A dermoscopic close-up of a skin lesion.
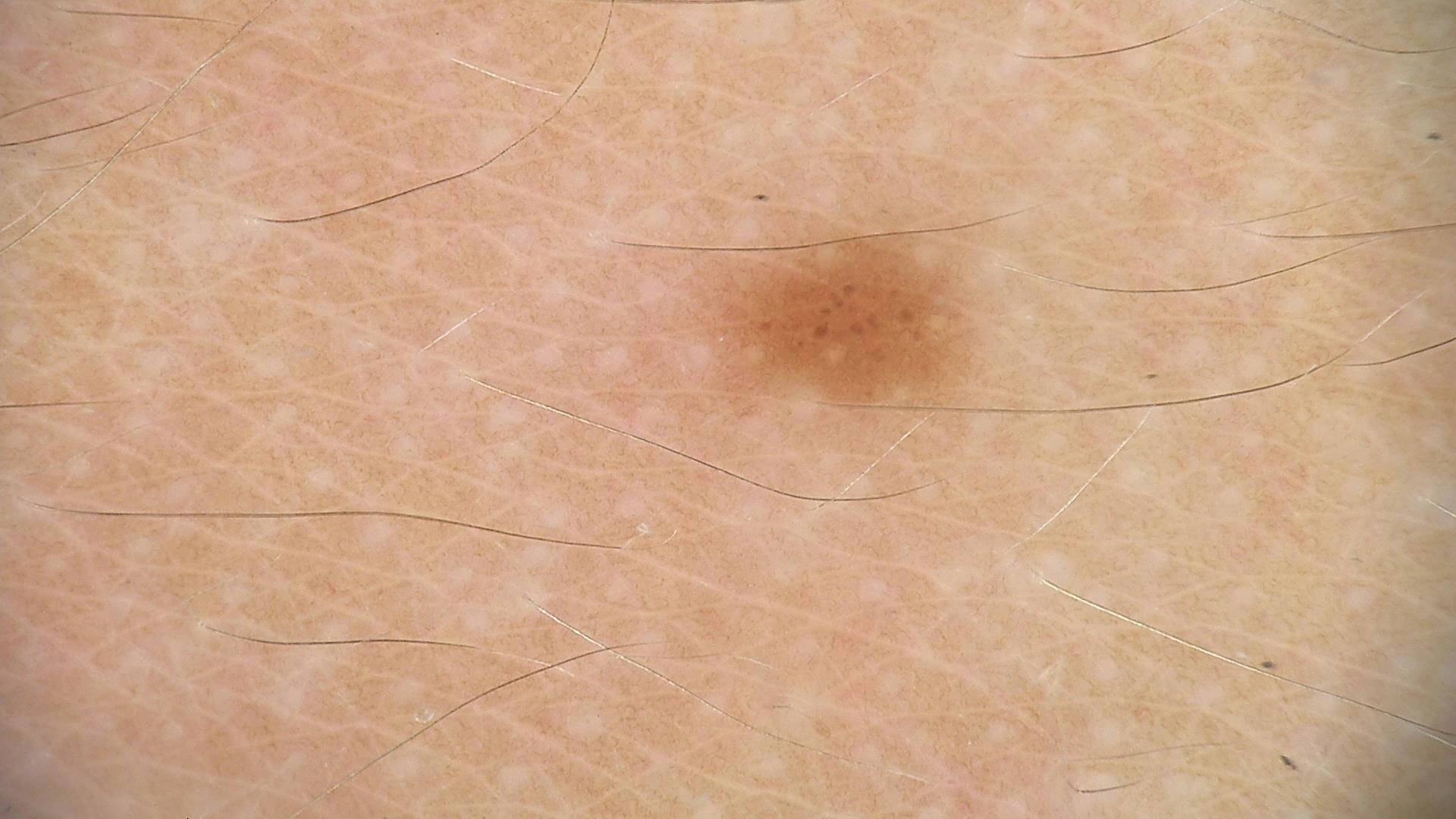Labeled as a dysplastic junctional nevus.